The lesion is described as fluid-filled. Female patient, age 50–59. The patient reports the condition has been present for less than one week. Self-categorized by the patient as a rash. The top or side of the foot is involved. Reported lesion symptoms include itching. The photo was captured at an angle — 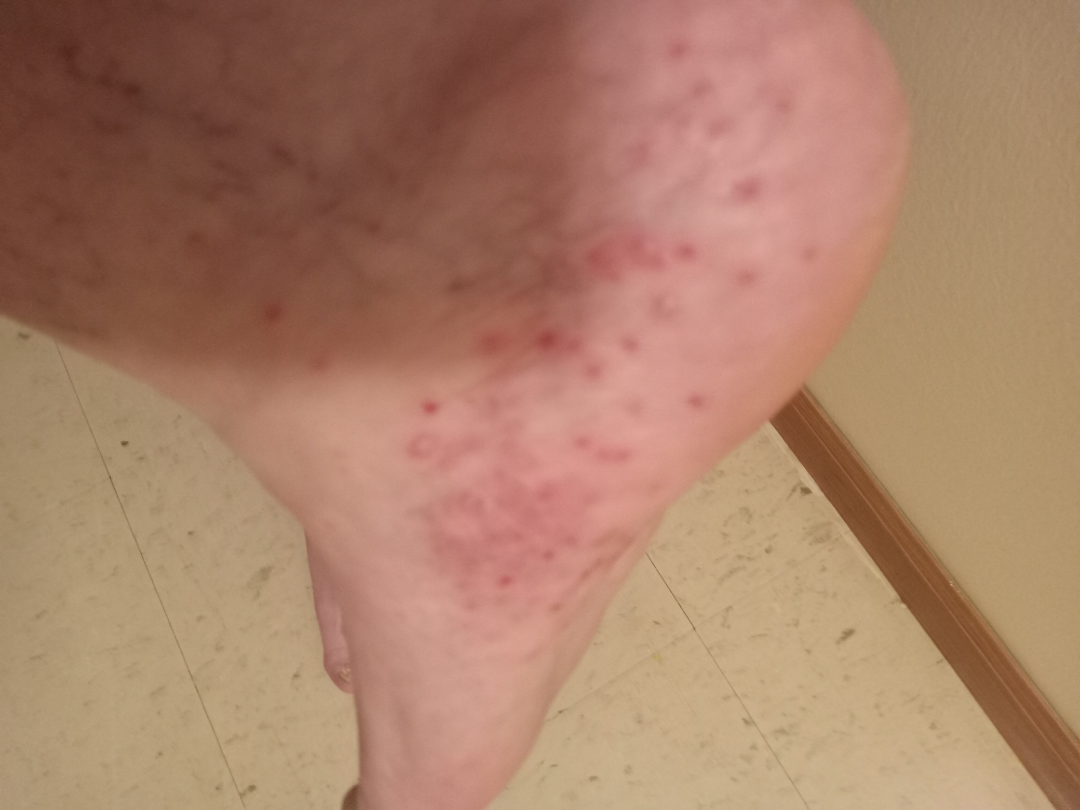diagnostic considerations=favoring Eczema; possibly Tinea; also on the differential is Psoriasis; less probable is Scabies